A dermatoscopic image of a skin lesion:
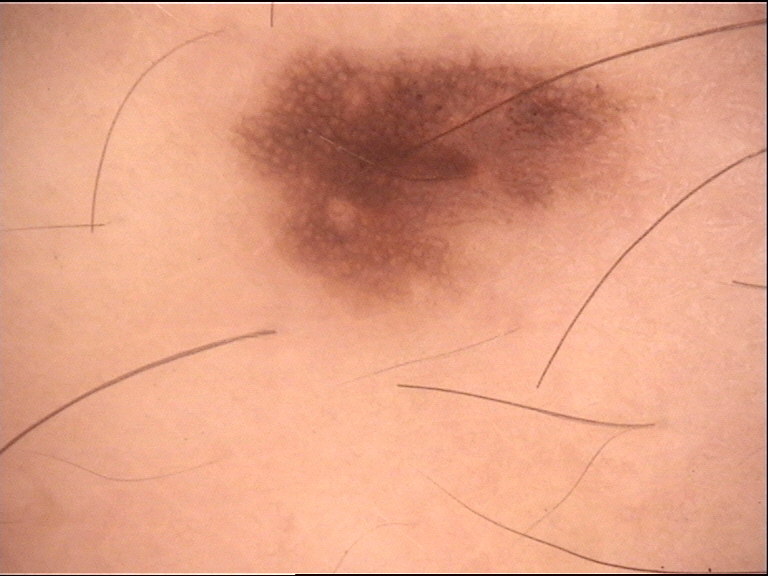Case:
- label — dysplastic junctional nevus (expert consensus)